A dermoscopic close-up of a skin lesion.
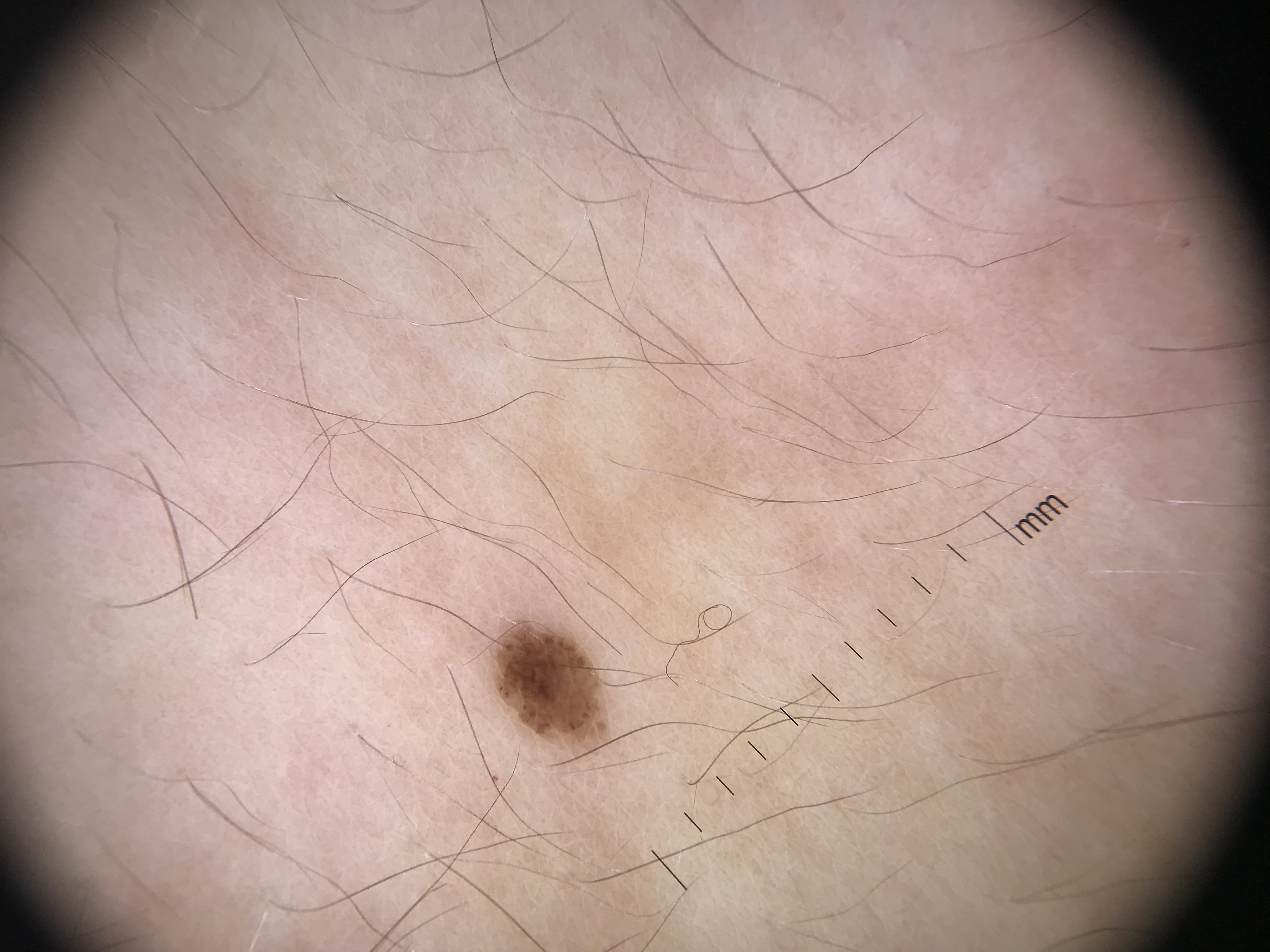Conclusion:
Labeled as a dysplastic junctional nevus.